A dermatoscopic image of a skin lesion — 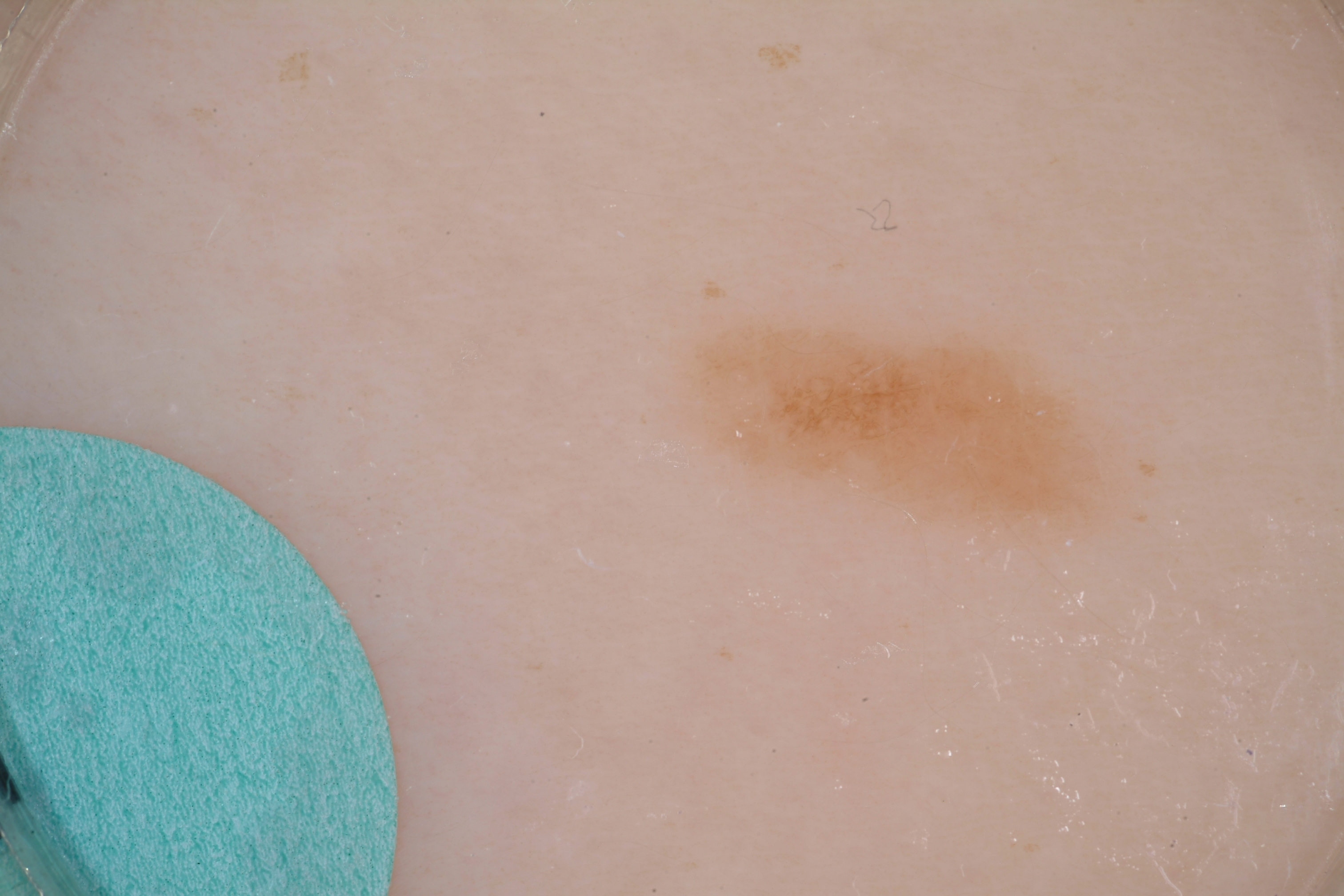| feature | finding |
|---|---|
| lesion bbox | bbox(686, 321, 1121, 539) |
| absent dermoscopic findings | globules and streaks |
| lesion extent | ~5% of the field |
| diagnostic label | a benign skin lesion |